A dermoscopic photograph of a skin lesion.
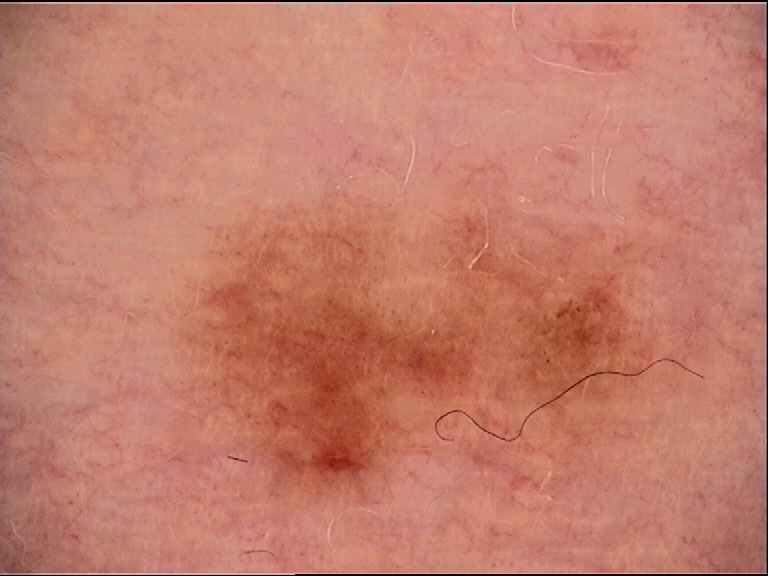Diagnosed as a benign lesion — a dysplastic junctional nevus.